A female patient 72 years of age. By history, prior malignancy (patient or family), tobacco use, prior skin cancer (patient or family), alcohol use, and no pesticide exposure. A clinical close-up photograph of a skin lesion — 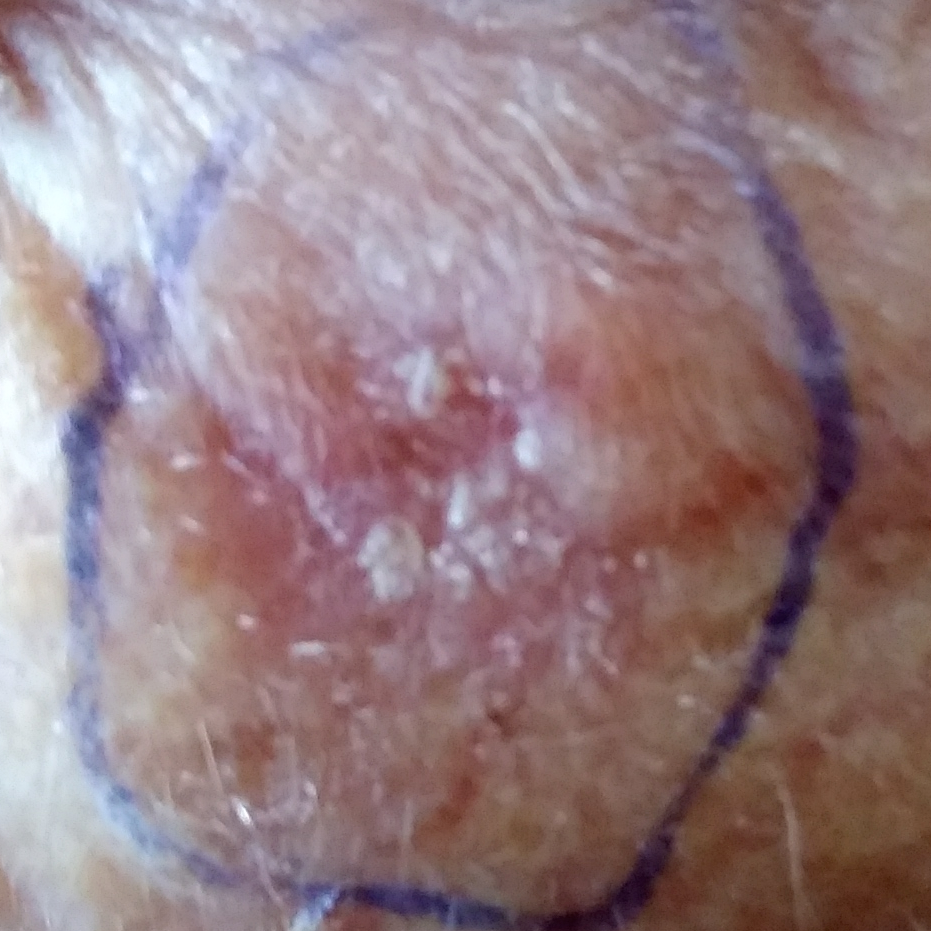The lesion is located on the face. Confirmed on histopathology as a basal cell carcinoma.